The leg, arm and top or side of the foot are involved · the photograph is a close-up of the affected area — 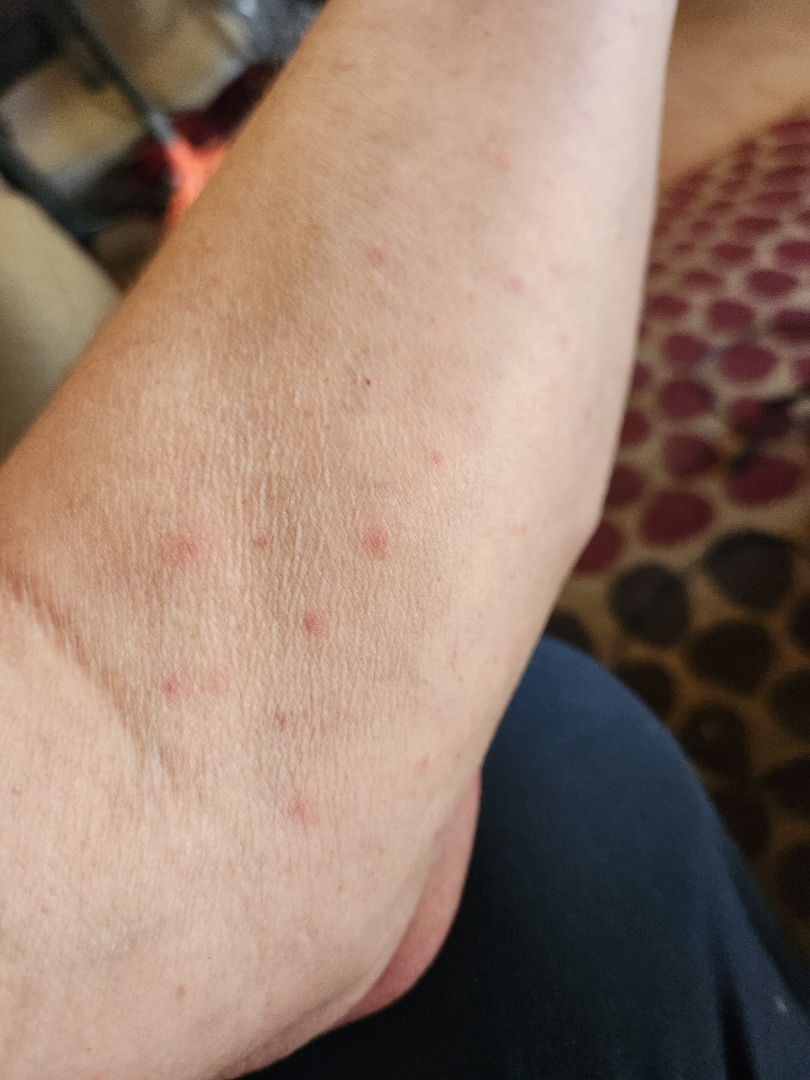Present for less than one week. Texture is reported as raised or bumpy. The lesion is associated with itching. Self-categorized by the patient as a rash. Scabies (considered); Folliculitis (considered); Insect Bite (remote).